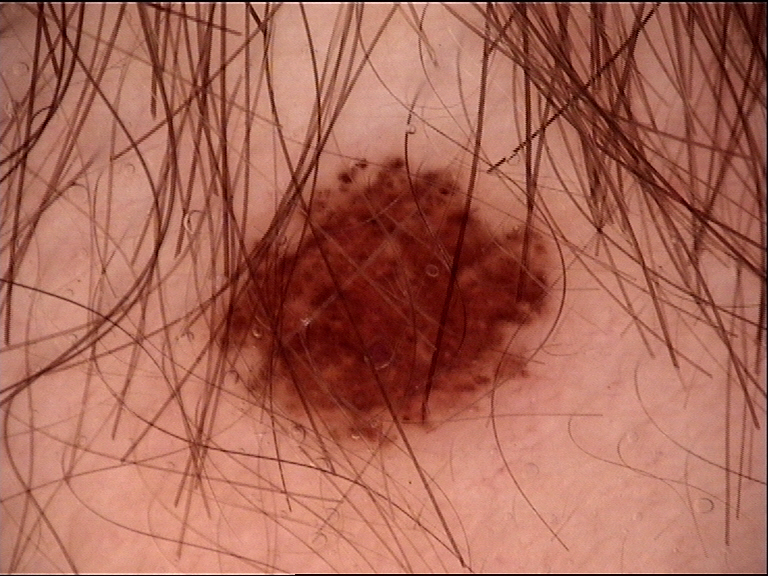Q: What kind of image is this?
A: dermatoscopy
Q: What is this lesion?
A: dysplastic junctional nevus (expert consensus)